A close-up photograph — 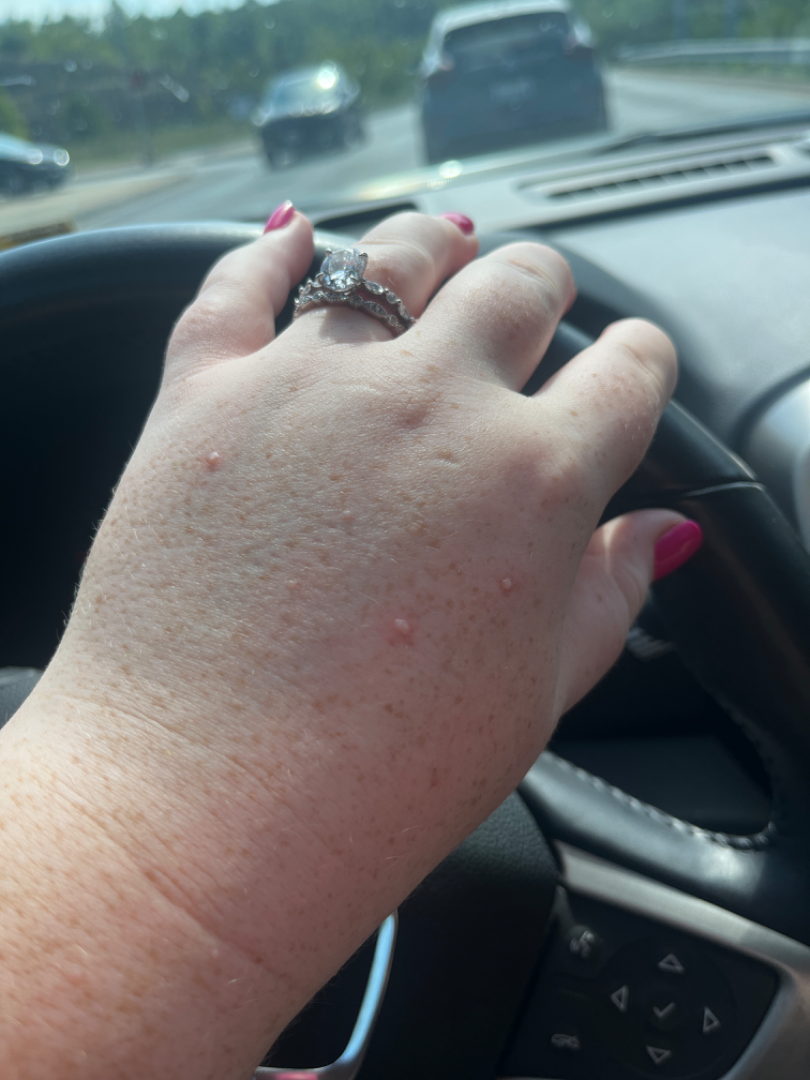Notes:
* assessment: unable to determine
* skin tone: Fitzpatrick II; non-clinician graders estimated a Monk Skin Tone of 2